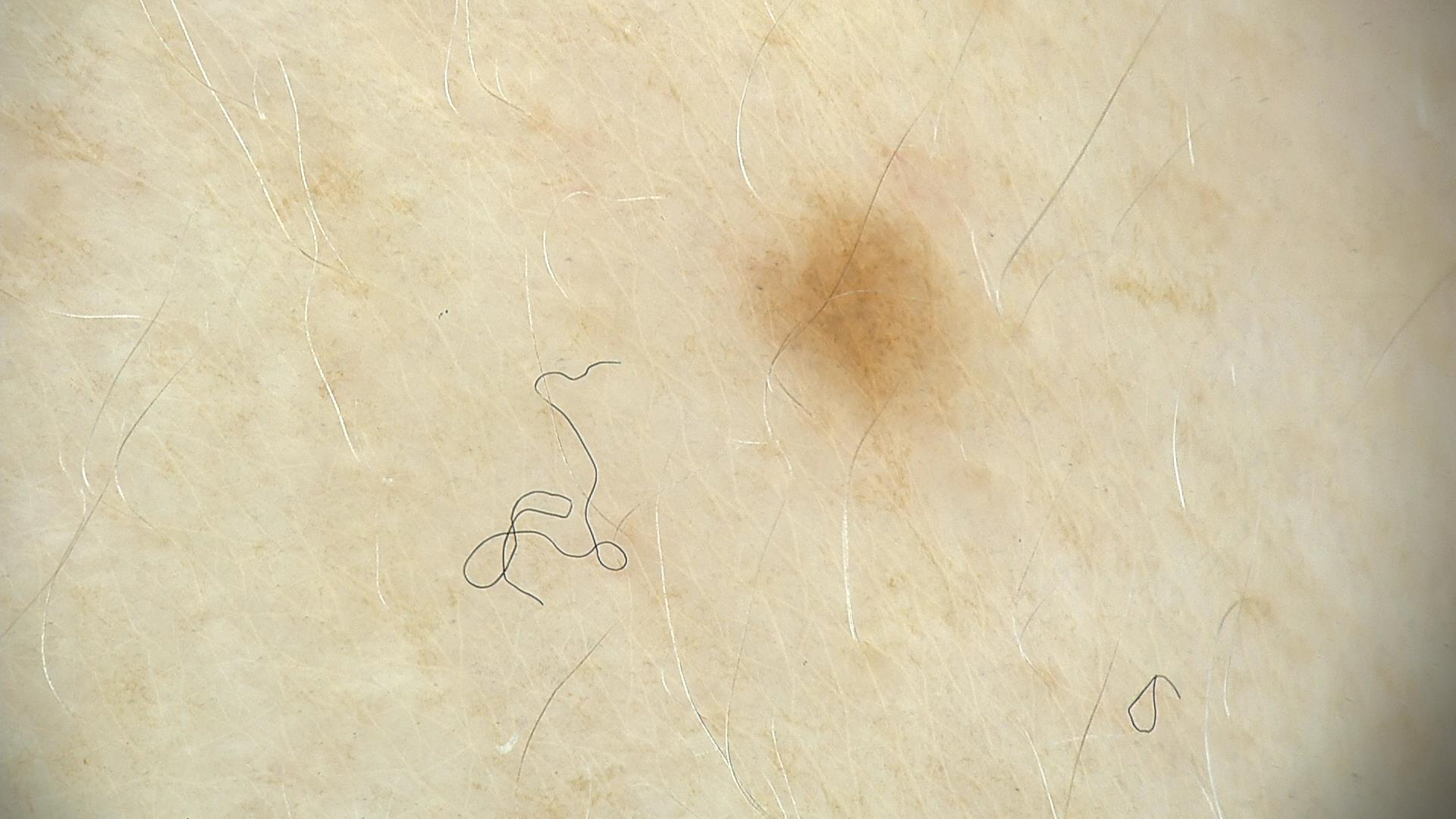{"image": "dermatoscopy", "lesion_type": {"main_class": "banal", "pattern": "junctional"}, "diagnosis": {"name": "junctional nevus", "code": "jb", "malignancy": "benign", "super_class": "melanocytic", "confirmation": "expert consensus"}}